The patient says their skin reddens with sun exposure. By self-report, a personal history of skin cancer, no family history of skin cancer, and no sunbed use. Acquired for a research image collection, with no referral diagnosis. A female patient 50 years old. The patient describes having a moderate number of moles.
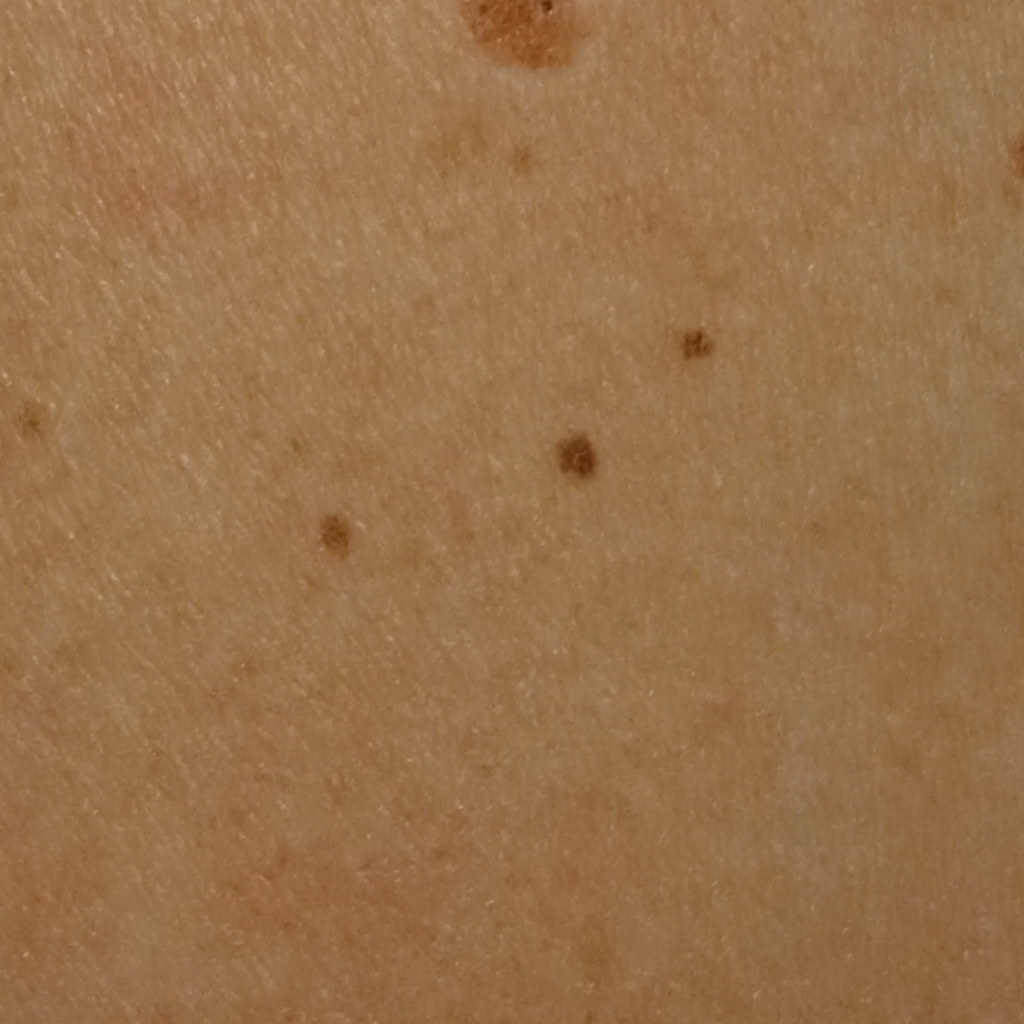Findings:
- location: an arm
- assessment: melanocytic nevus (dermatologist consensus)